The lesion involves the leg and arm, close-up view, skin tone: FST IV; lay reviewers estimated MST 3–4.
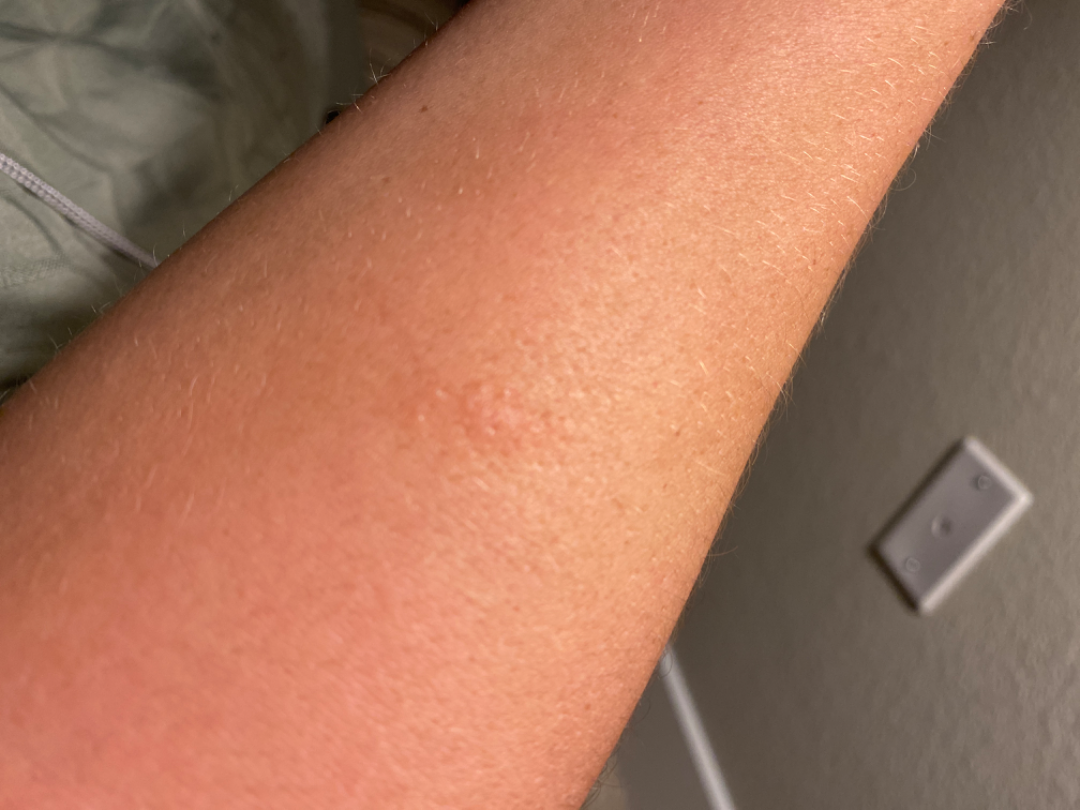The skin findings could not be characterized from the image.